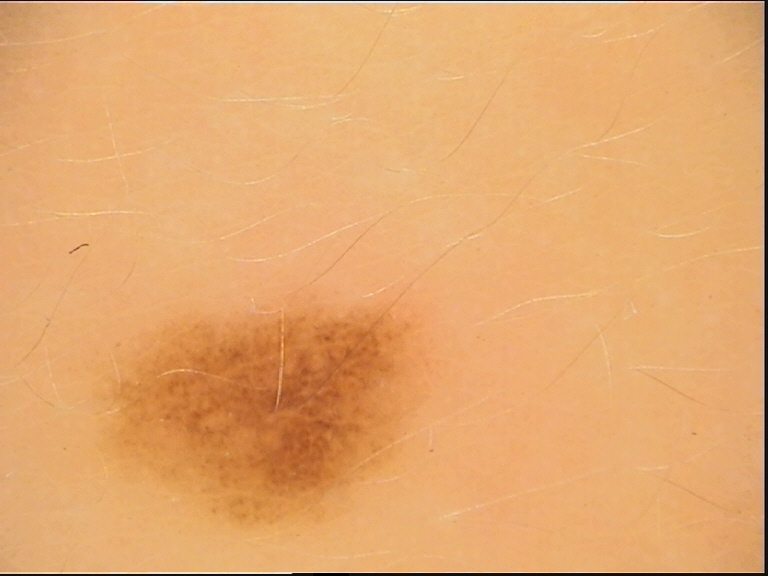diagnosis = dysplastic junctional nevus (expert consensus)